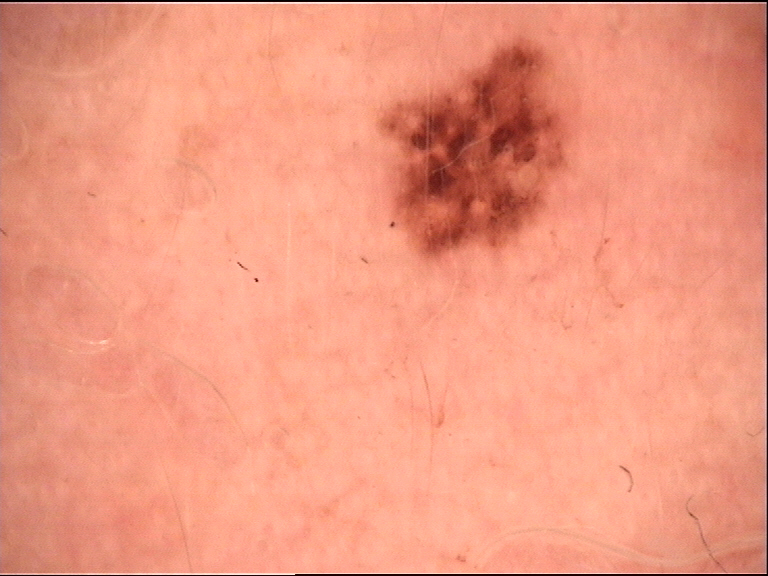diagnostic label=junctional nevus (expert consensus).